The condition has been present for one to four weeks, texture is reported as flat, the photograph was taken at an angle, the lesion involves the back of the torso, no constitutional symptoms were reported, reported lesion symptoms include bothersome appearance: 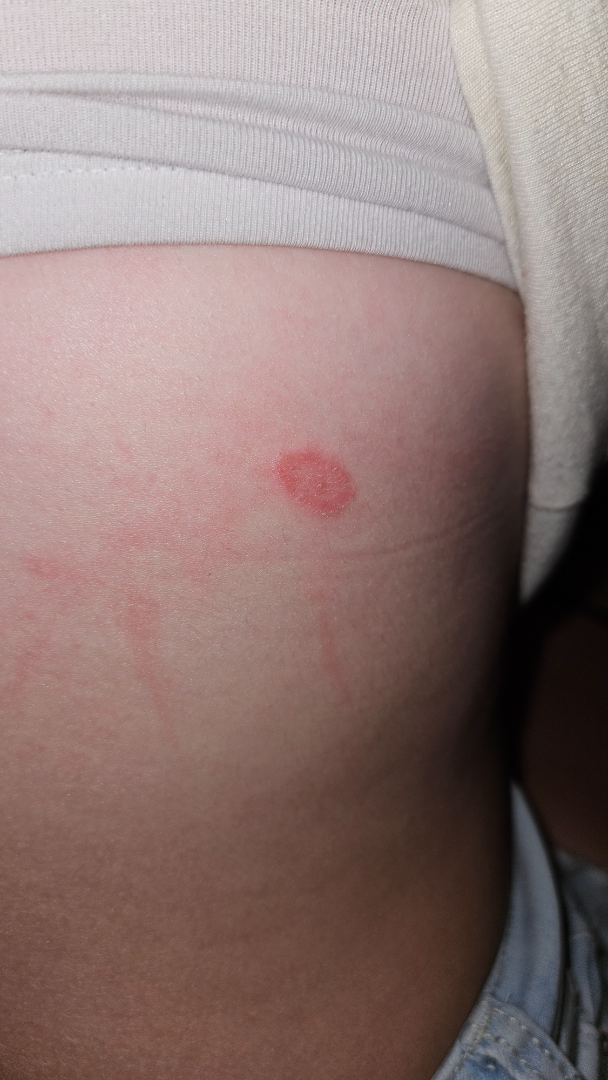Q: What is the dermatologist's impression?
A: Tinea (favored)